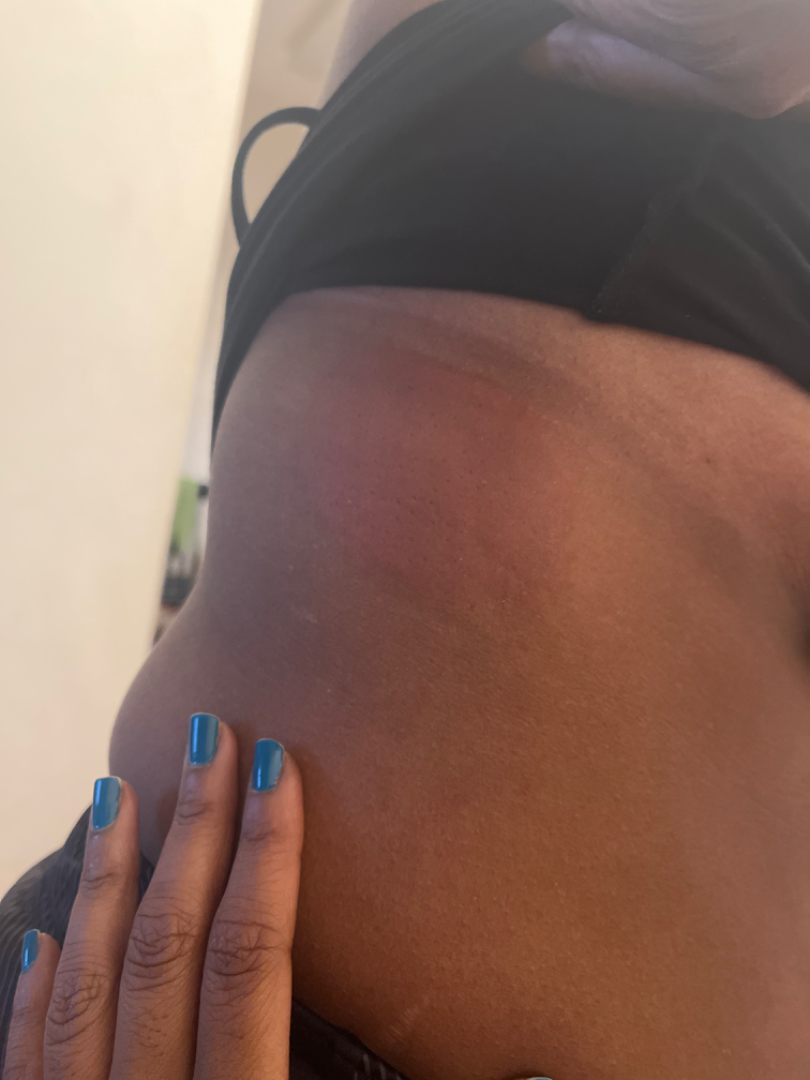Patient information: The subject is 50–59, female. The contributor notes the lesion is fluid-filled and raised or bumpy. Close-up view. The patient reported no systemic symptoms. The patient described the issue as a rash. Review: Three dermatologists independently reviewed the case: the impression was split between Urticaria and Erythema migrans; a remote consideration is Allergic Contact Dermatitis.